A dermatoscopic image of a skin lesion.
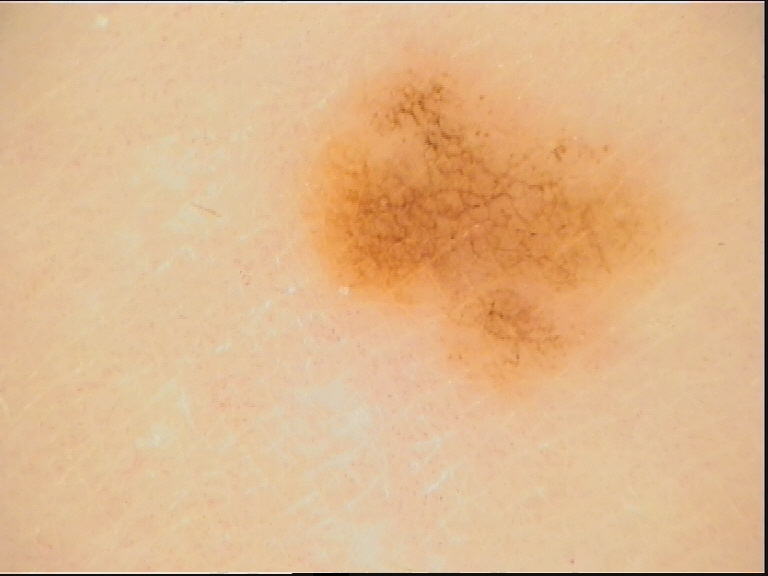Impression: Consistent with a benign lesion — a dysplastic junctional nevus.